A dermatoscopic image of a skin lesion.
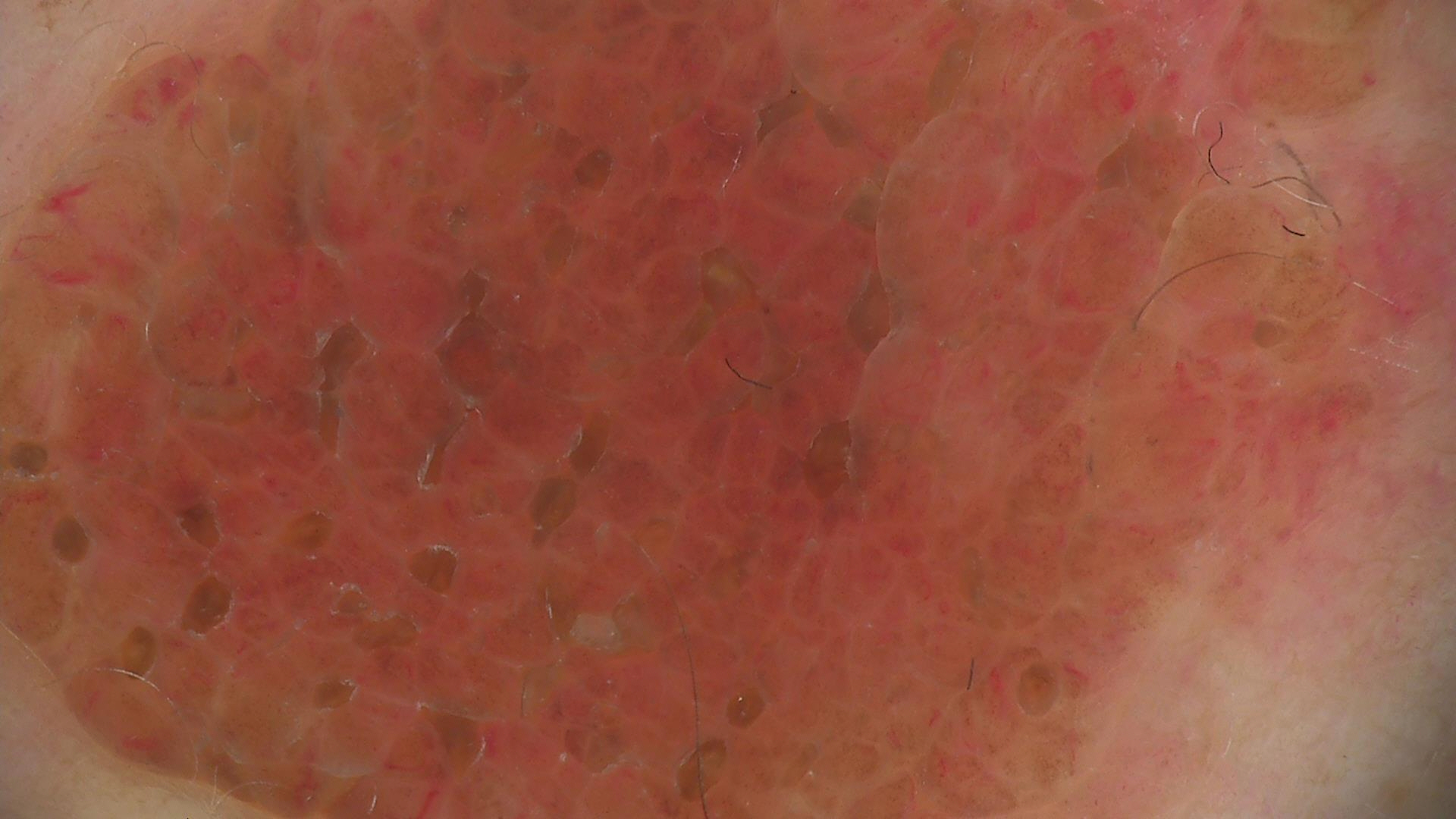class: dermal nevus (expert consensus).